The subject is female; the lesion involves the leg; this is a close-up image.
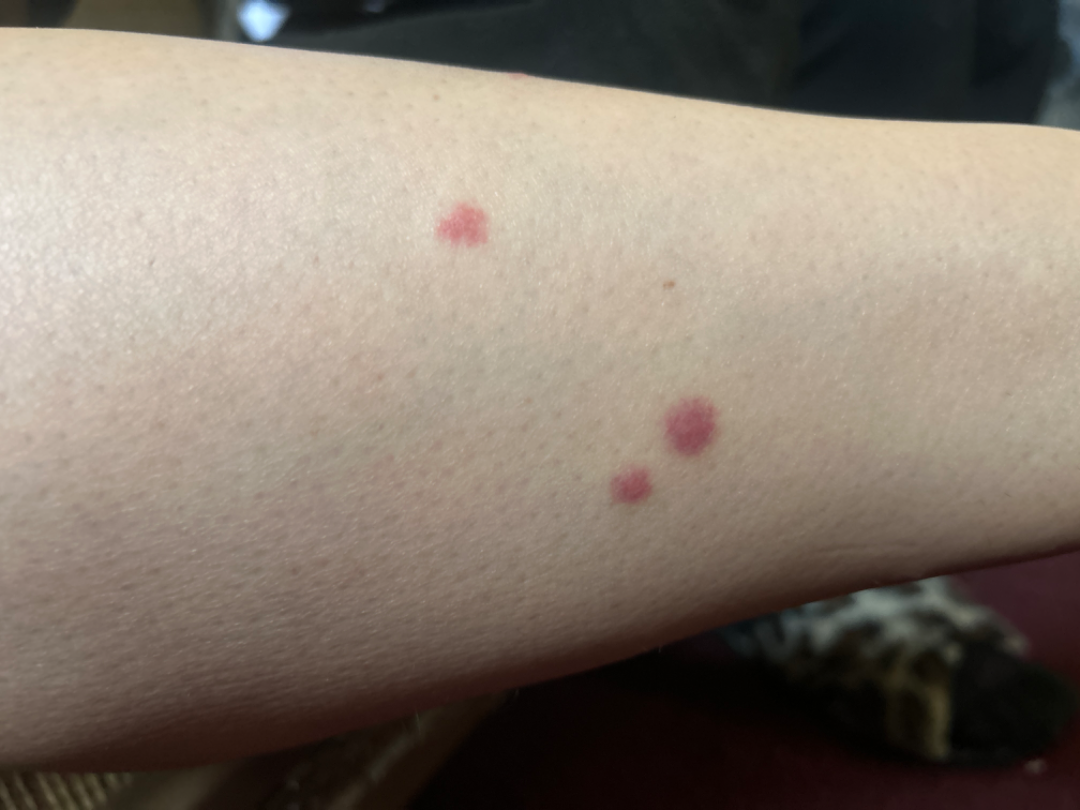No associated systemic symptoms reported. The contributor reports bothersome appearance and burning. The condition has been present for less than one week. The lesion is described as raised or bumpy. On photographic review by a dermatologist: the differential includes Insect Bite and Leukocytoclastic Vasculitis, with no clear leading consideration.